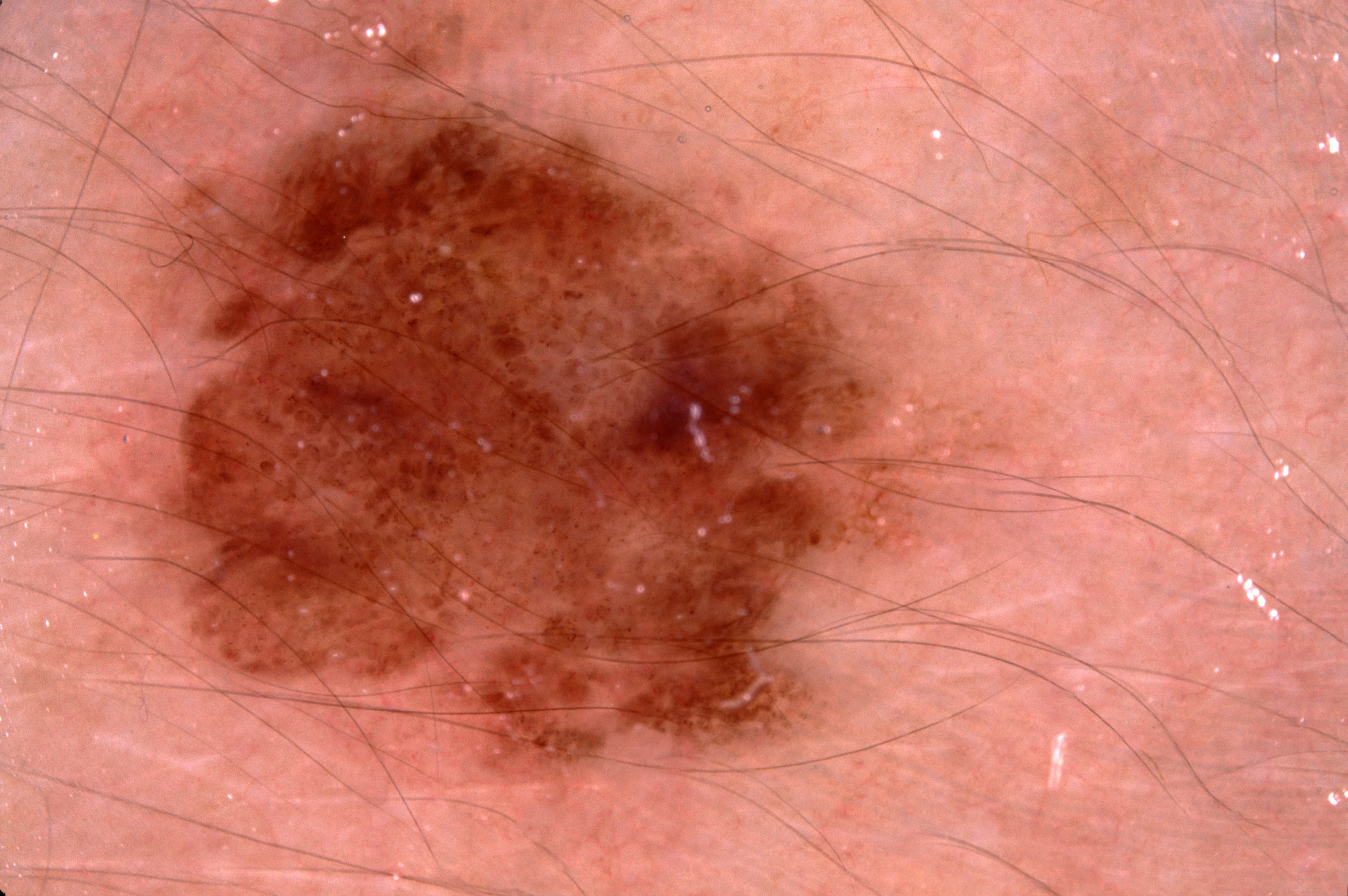modality: dermoscopy of a skin lesion
lesion bbox: box(138, 88, 929, 779)
size: large
dermoscopic pattern: milia-like cysts, negative network, and pigment network
impression: a melanocytic nevus